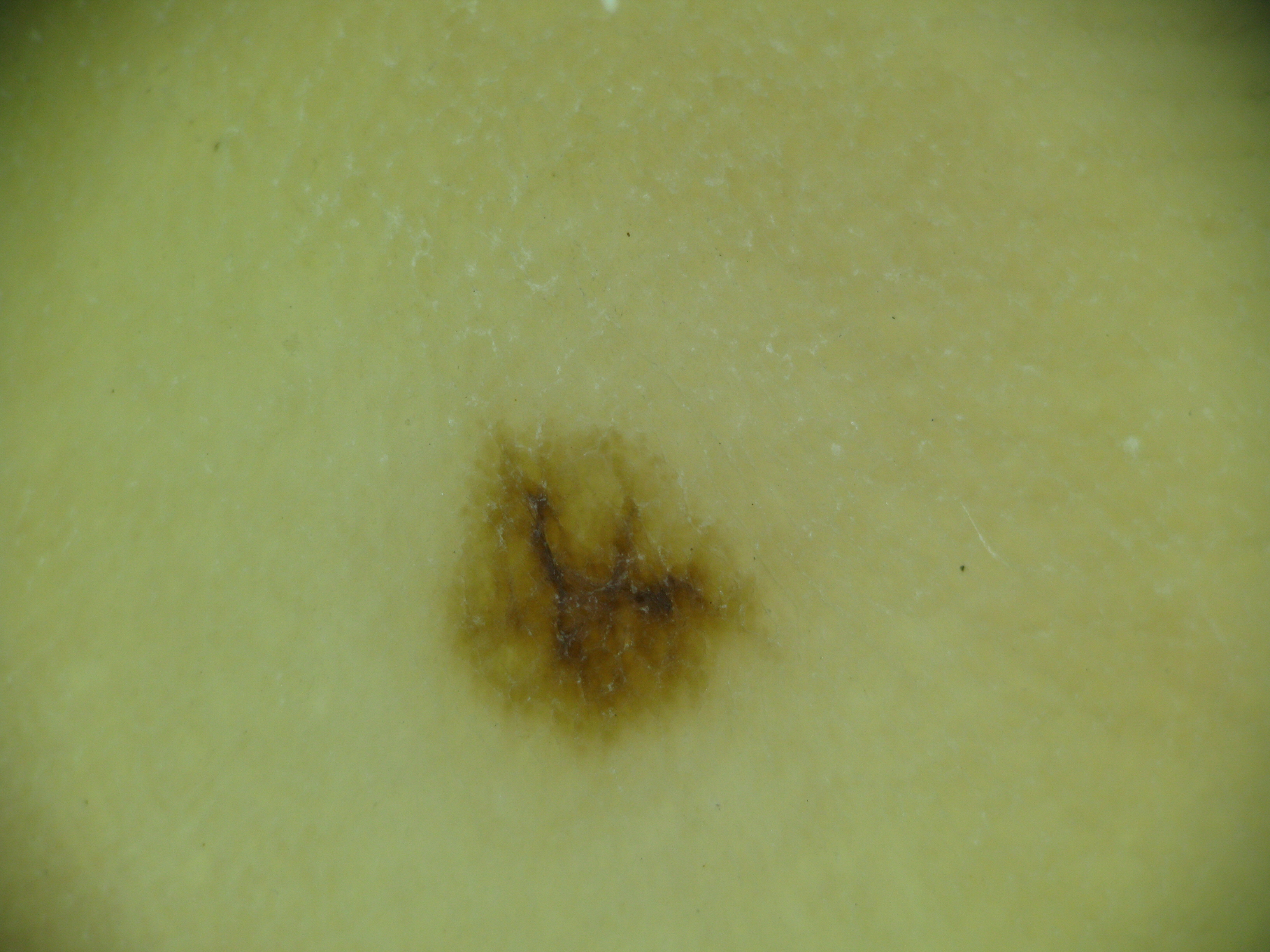Q: What was the diagnostic impression?
A: acral junctional nevus (expert consensus)